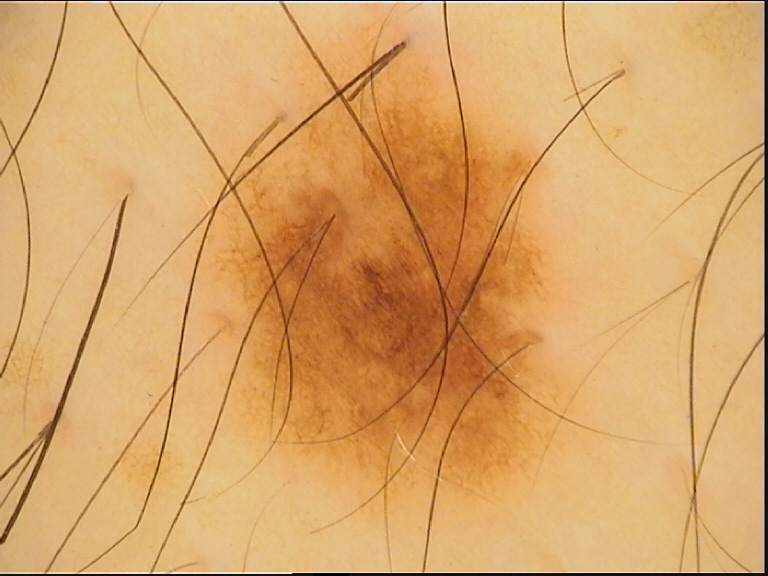Findings:
– label · dysplastic junctional nevus (expert consensus)